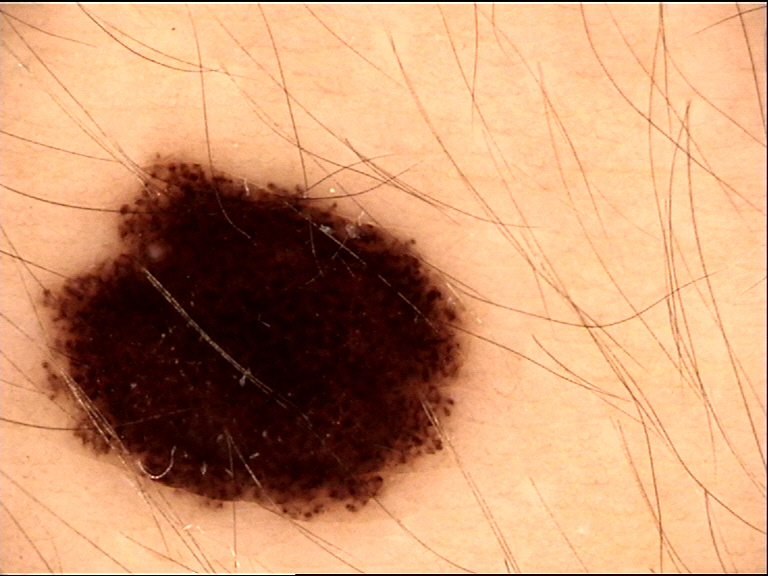A dermatoscopic image of a skin lesion.
Diagnosed as a benign lesion — a dysplastic compound nevus.